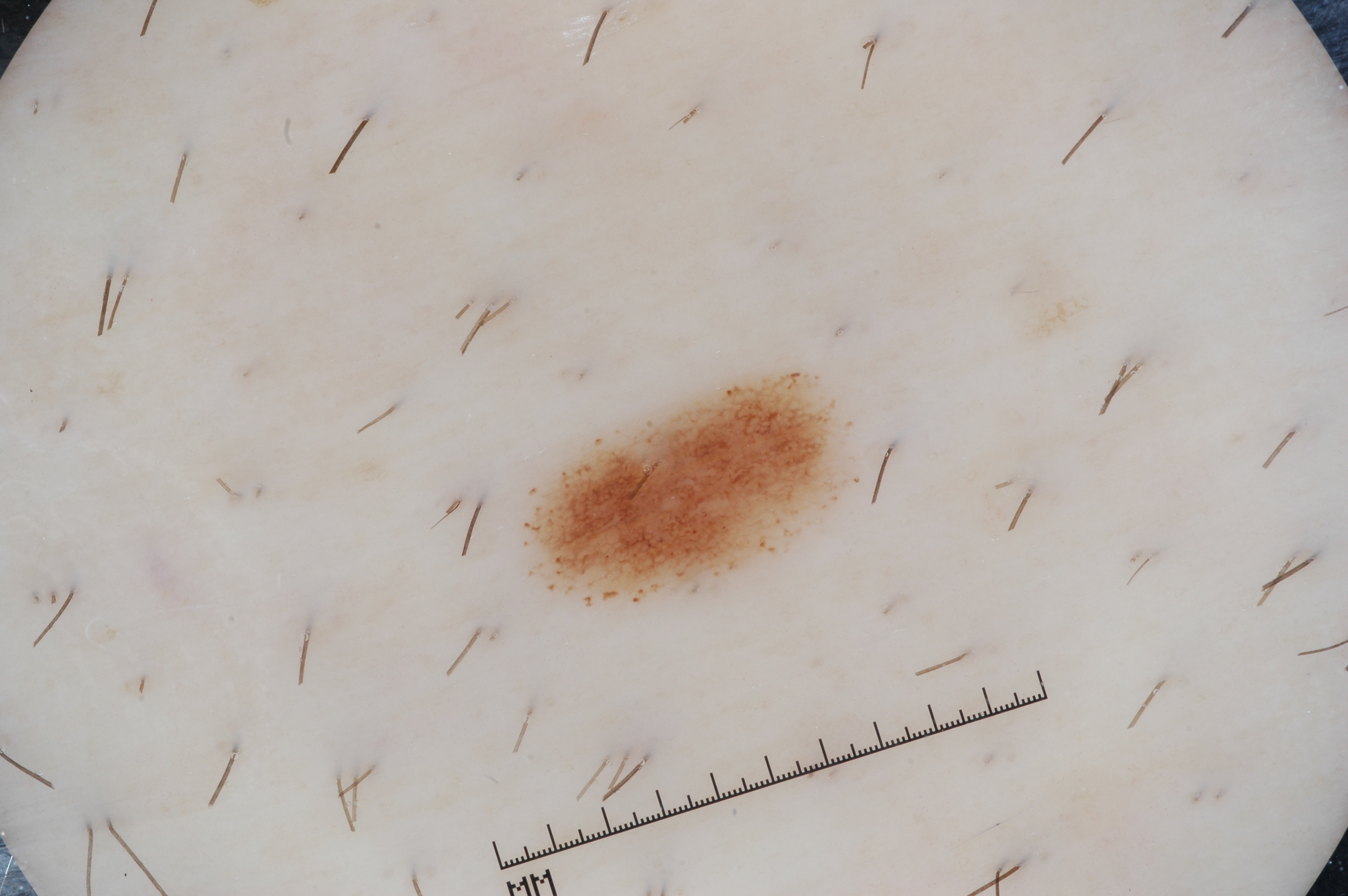Case summary:
A dermoscopy image of a single skin lesion. The lesion spans <box>521, 366, 861, 607</box>. On dermoscopy, the lesion shows pigment network, with no streaks, negative network, or milia-like cysts.
Impression:
The lesion was assessed as a melanocytic nevus.